The photo was captured at a distance · located on the leg:
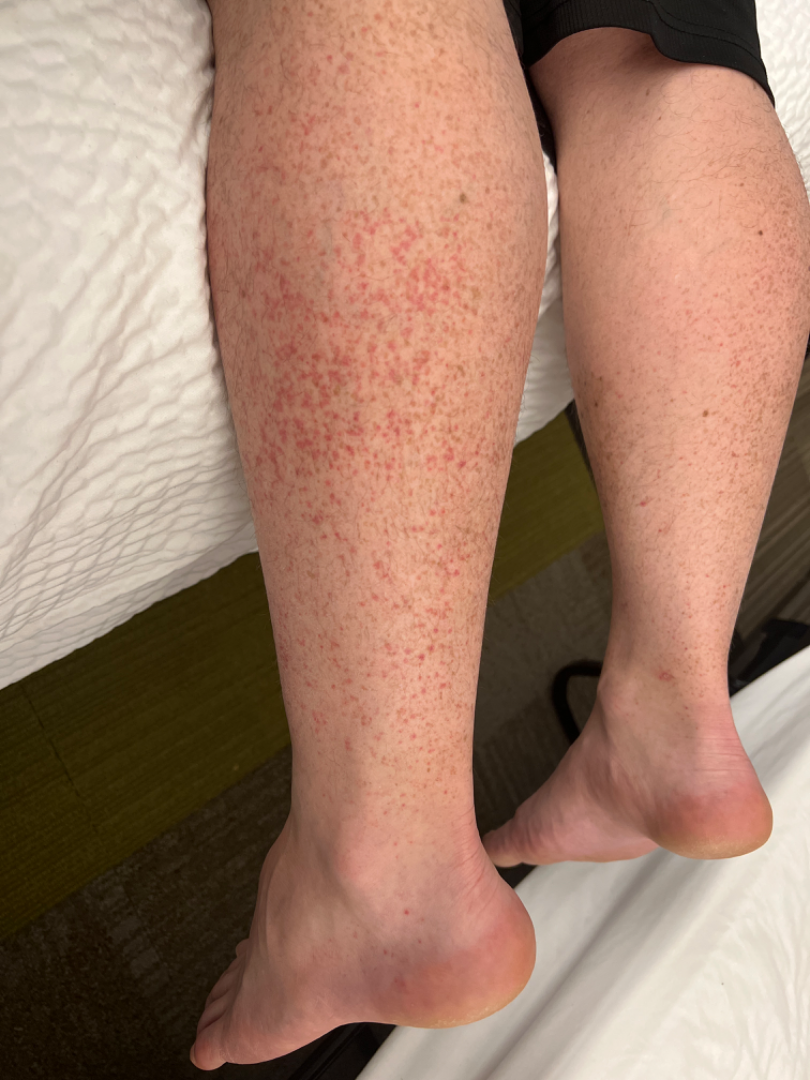The patient indicates the lesion is flat. Fitzpatrick III; lay graders estimated Monk Skin Tone 2 or 3. The patient reported no relevant symptoms from the lesion. On dermatologist assessment of the image, in keeping with Leukocytoclastic Vasculitis.